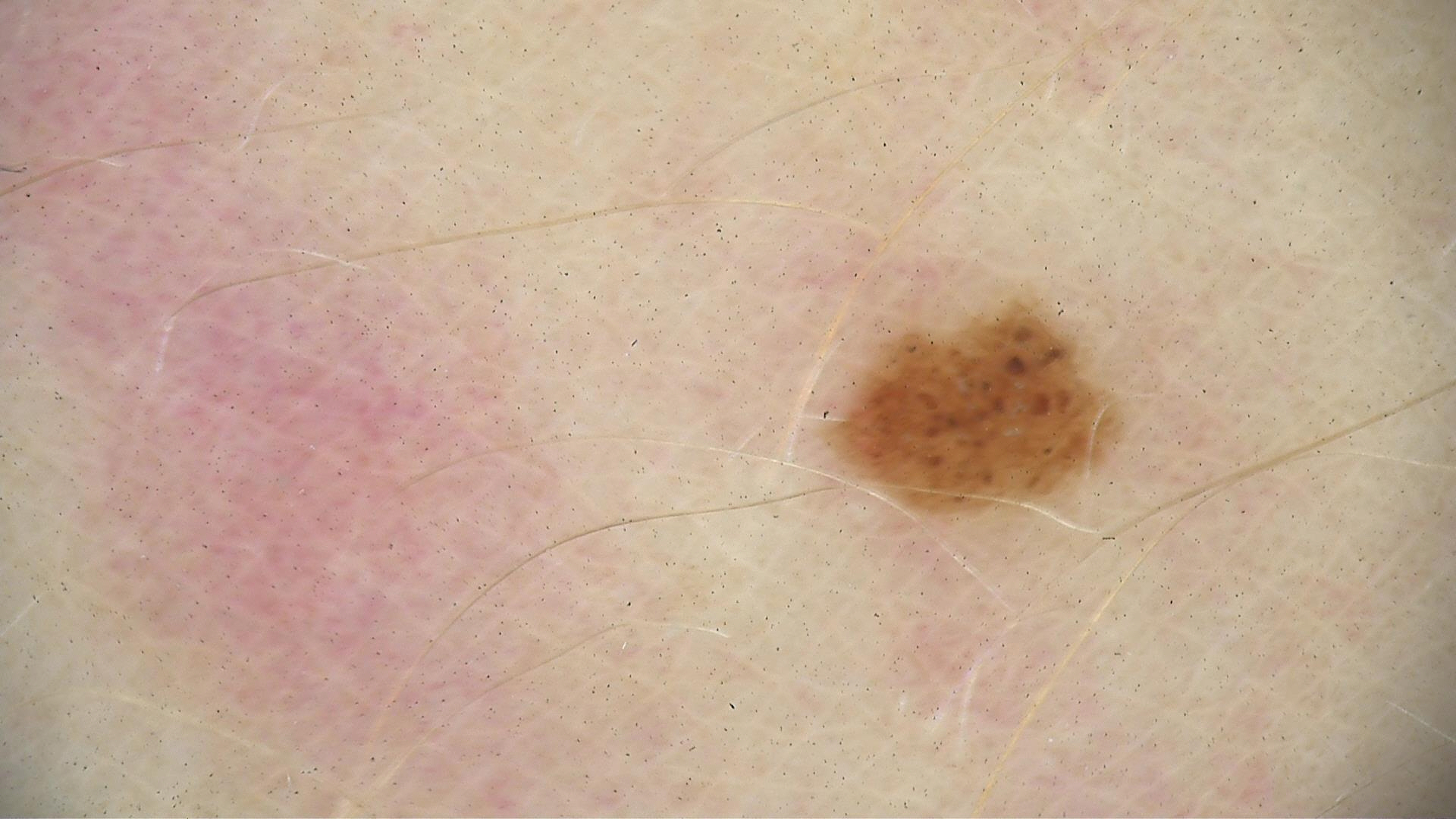Summary:
A dermoscopy image of a single skin lesion.
Impression:
The diagnostic label was a benign lesion — a dysplastic junctional nevus.